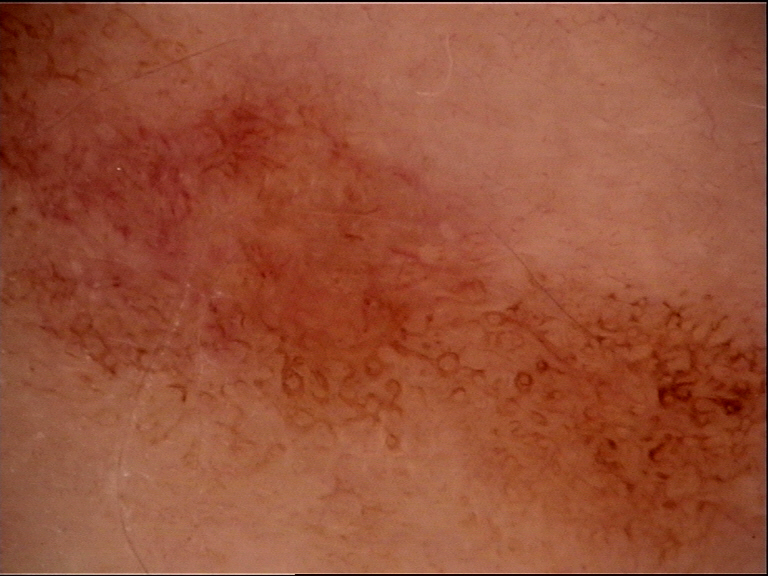Dermoscopy of a skin lesion. Consistent with a benign lesion — a dysplastic junctional nevus.